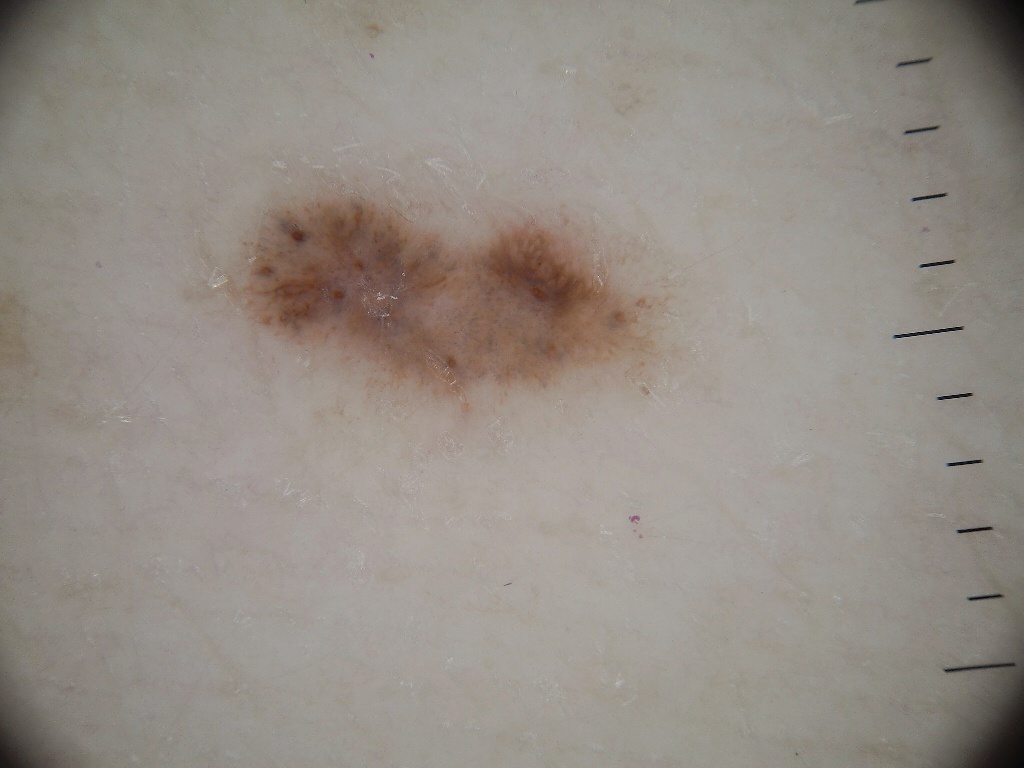imaging: dermoscopic image; lesion location: 221/170/651/411; impression: a melanocytic nevus, a benign skin lesion.